Male contributor, age 40–49 · an image taken at an angle:
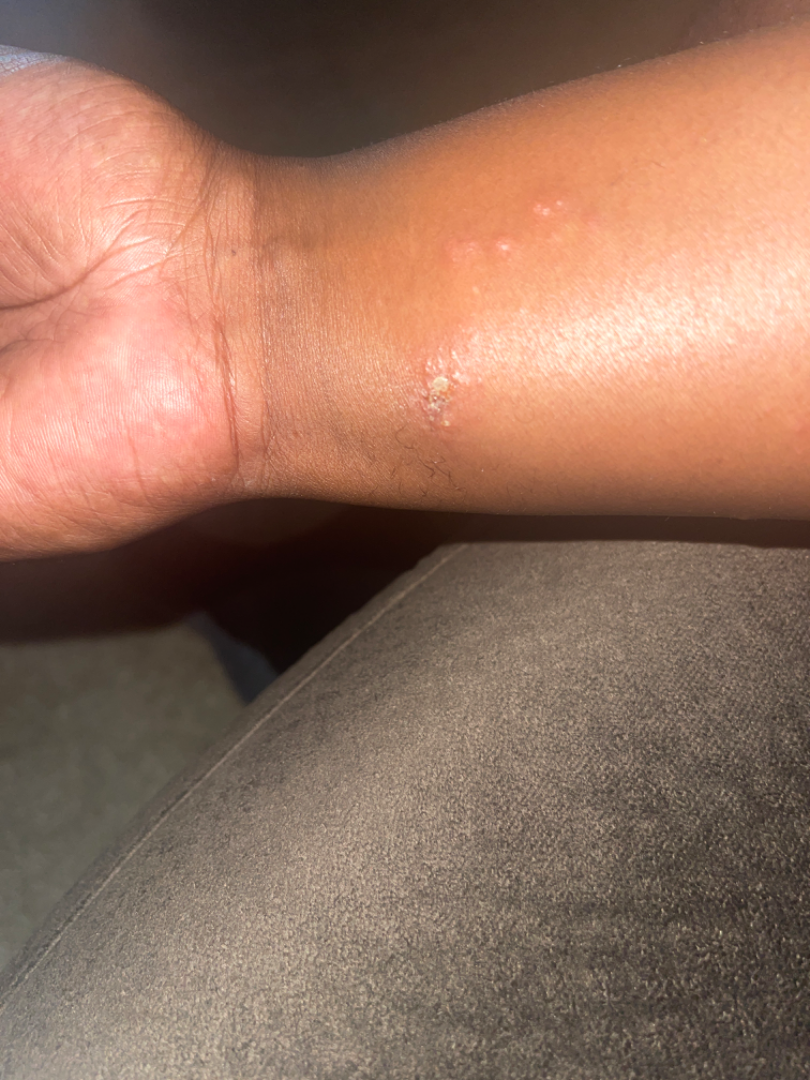The patient indicates the lesion is fluid-filled, rough or flaky and raised or bumpy.
Reported duration is less than one week.
Reported lesion symptoms include bothersome appearance, enlargement and itching.
Fitzpatrick V; human graders estimated Monk skin tone scale 5 or 6 (two reviewer pools).
Self-categorized by the patient as a rash.
No constitutional symptoms were reported.
The reviewing dermatologist's impression was: the differential, in no particular order, includes Scabies and Molluscum Contagiosum; less probable is Perforating dermatosis.